A dermoscopic image of a skin lesion; a female subject, aged approximately 5: 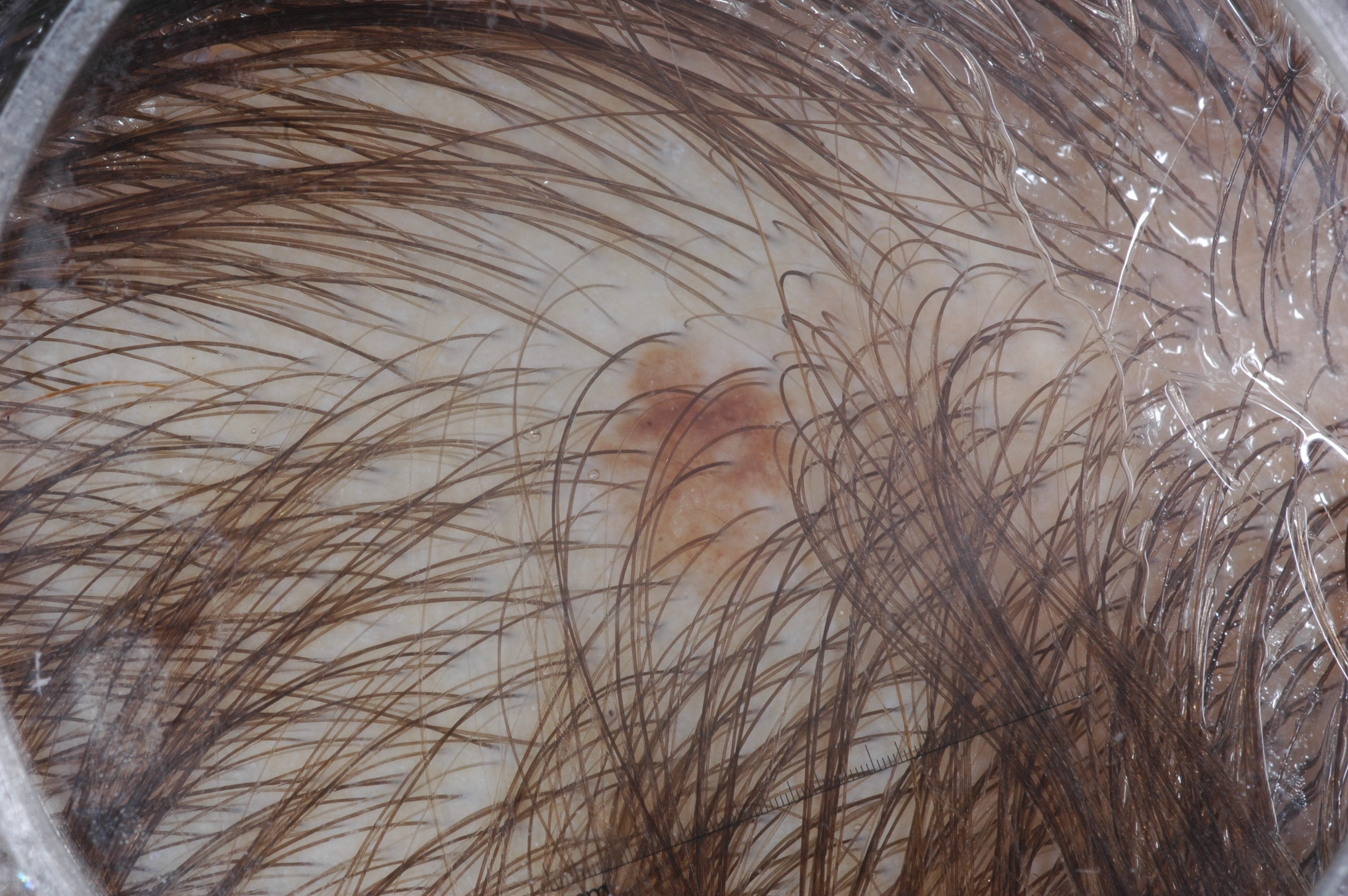The lesion takes up about 5% of the image. As (left, top, right, bottom), the lesion is bounded by 579 338 834 655. Dermoscopically, the lesion shows no streaks, negative network, milia-like cysts, or pigment network. The lesion was assessed as a melanocytic nevus.